A dermatoscopic image of a skin lesion: 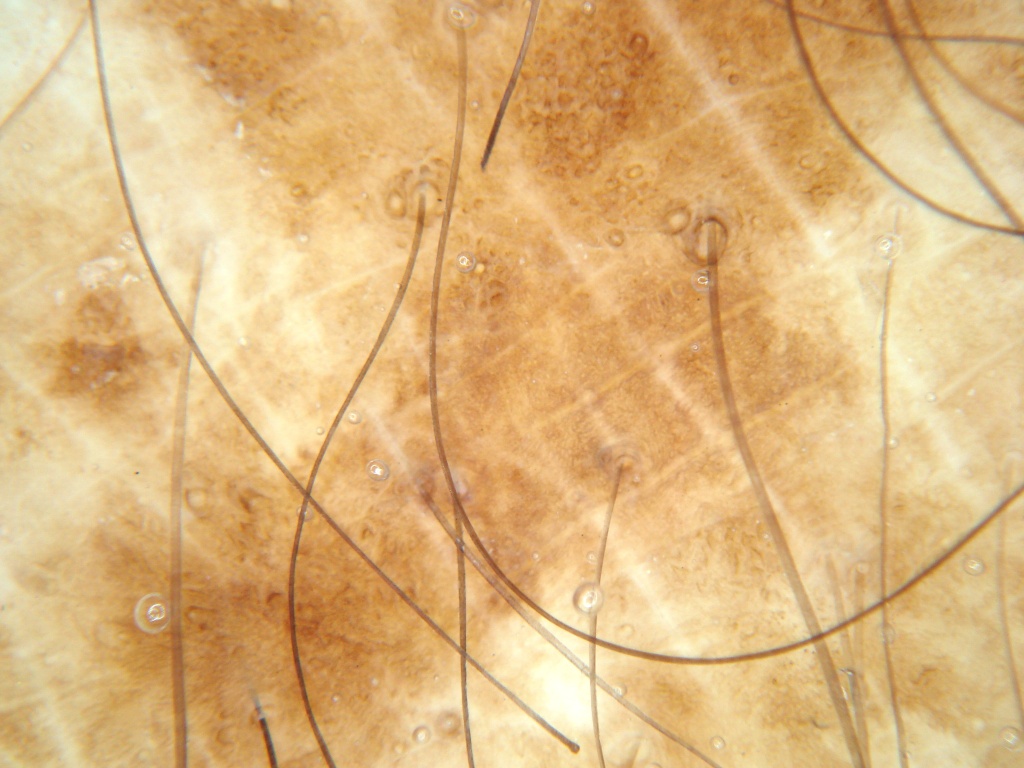Dermoscopic examination shows no globules or streaks.
The lesion spans essentially the entire dermoscopic field.
The lesion was assessed as a benign lesion.